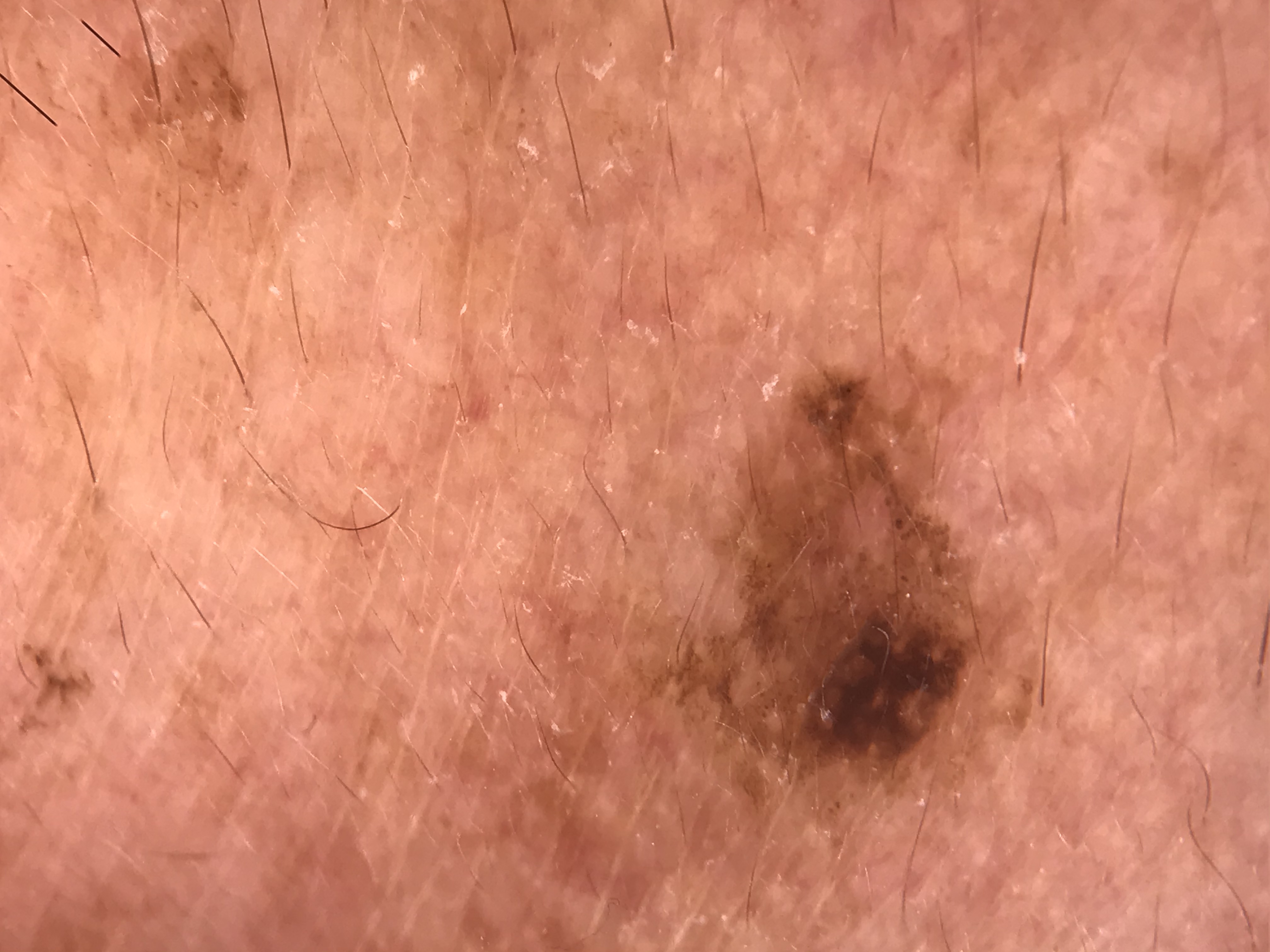| feature | finding |
|---|---|
| label | seborrheic keratosis (expert consensus) |